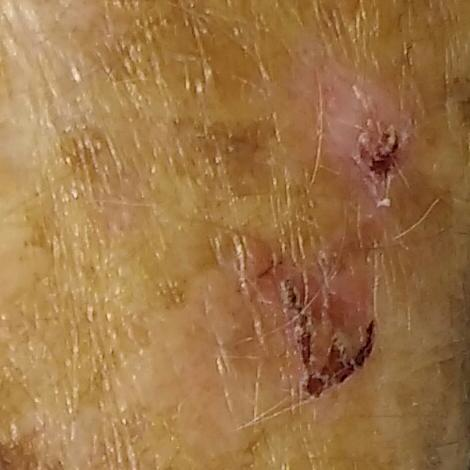Clinical context:
The patient was assessed as Fitzpatrick skin type II. A female patient aged 82. A smartphone photograph of a skin lesion. The lesion is on a forearm. Measuring about 9 × 7 mm. The patient describes that the lesion has bled and itches, but is not elevated and does not hurt.
Impression:
The consensus clinical diagnosis was a lesion of indeterminate malignant potential — an actinic keratosis.